The chart records a prior melanoma. A female patient approximately 70 years of age. A contact-polarized dermoscopy image of a skin lesion. The patient was assessed as Fitzpatrick II — 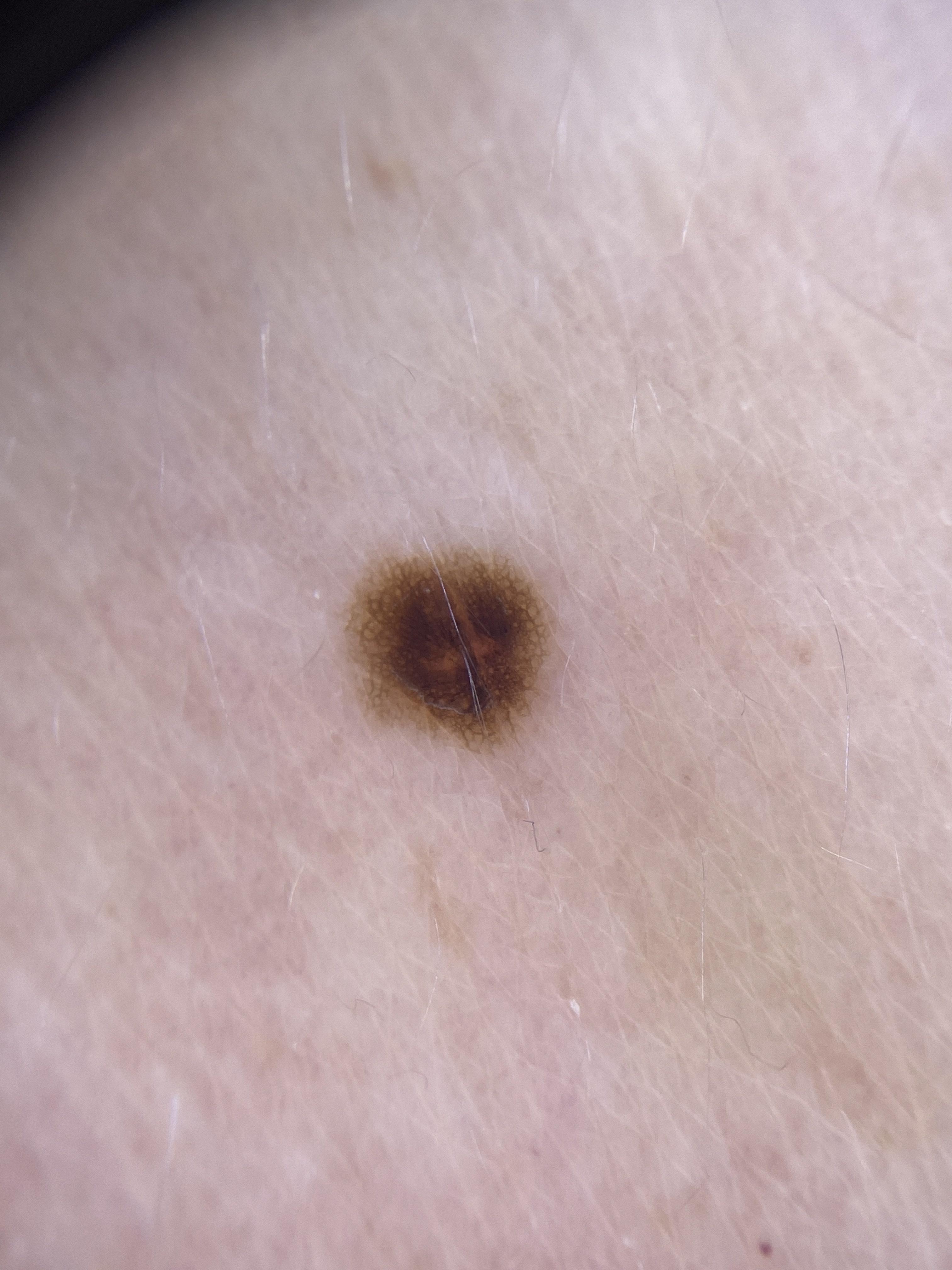Notes:
* anatomic site · an upper extremity
* diagnosis · Nevus (clinical impression)